A smartphone photograph of a skin lesion · a female patient age 86 · the chart records prior malignancy (patient or family) and no prior skin cancer (patient or family).
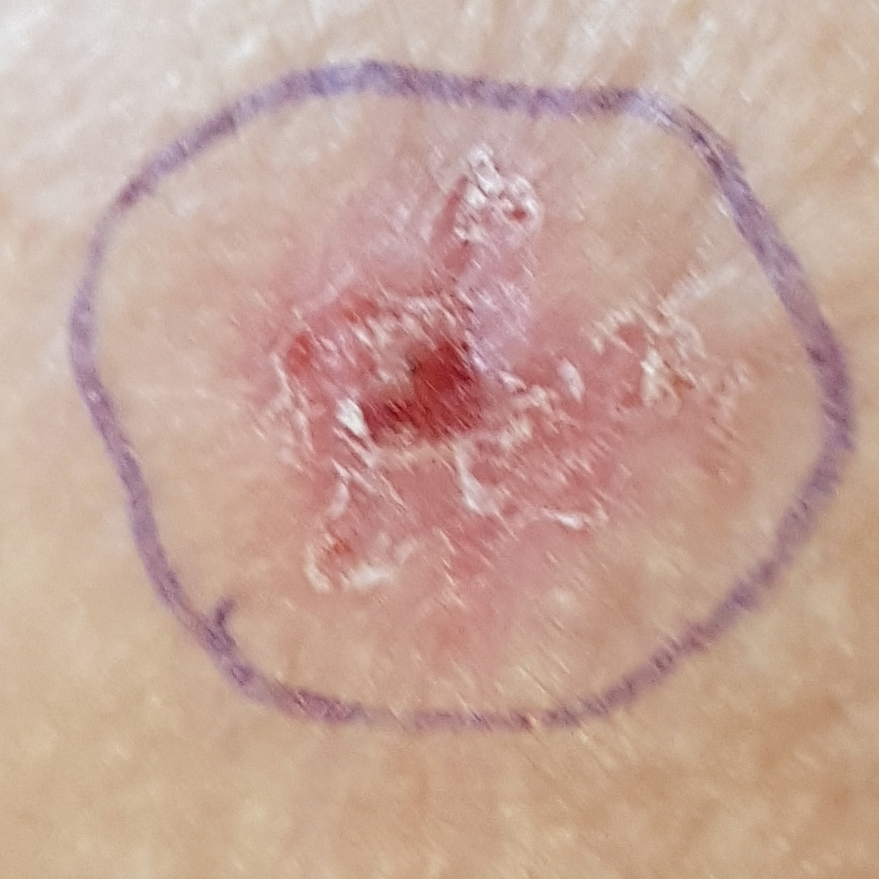| key | value |
|---|---|
| anatomic site | an arm |
| diameter | 14 × 12 mm |
| diagnosis | basal cell carcinoma (biopsy-proven) |